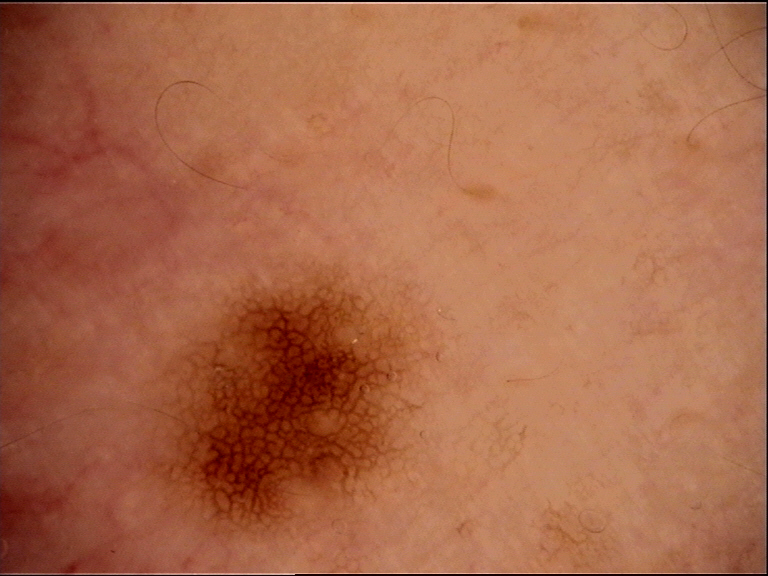Summary: A dermatoscopic image of a skin lesion. Impression: Classified as a benign lesion — a dysplastic junctional nevus.